A male subject aged 63-67; this is a dermoscopic photograph of a skin lesion.
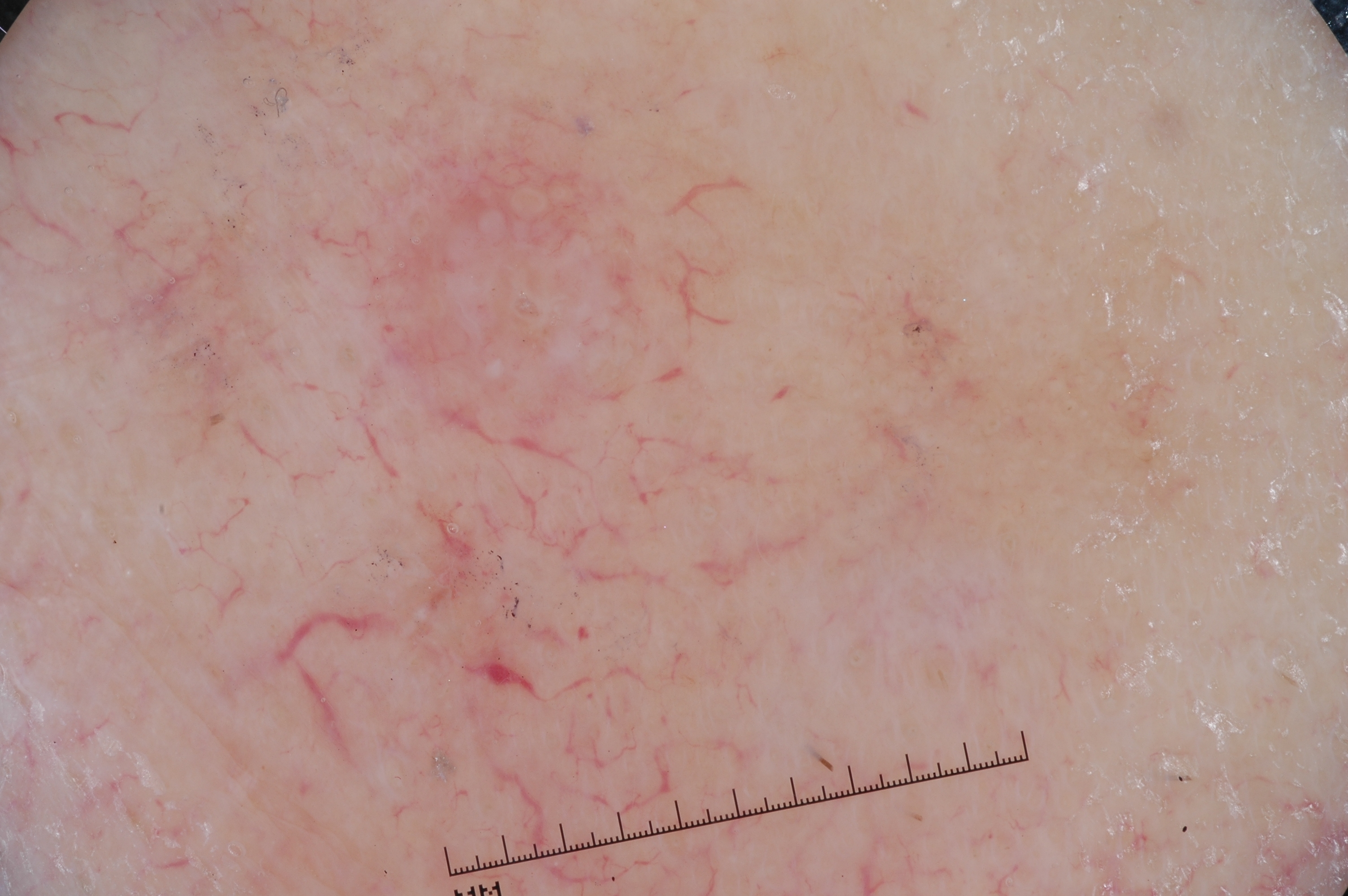In (x1, y1, x2, y2) order, the lesion is located at box(106, 0, 1211, 895). The dermoscopic pattern shows no streaks, negative network, milia-like cysts, or pigment network. Expert review diagnosed this as a seborrheic keratosis.